The patient was assessed as Fitzpatrick phototype III · a female patient in their mid-80s · a clinical photograph showing a skin lesion: 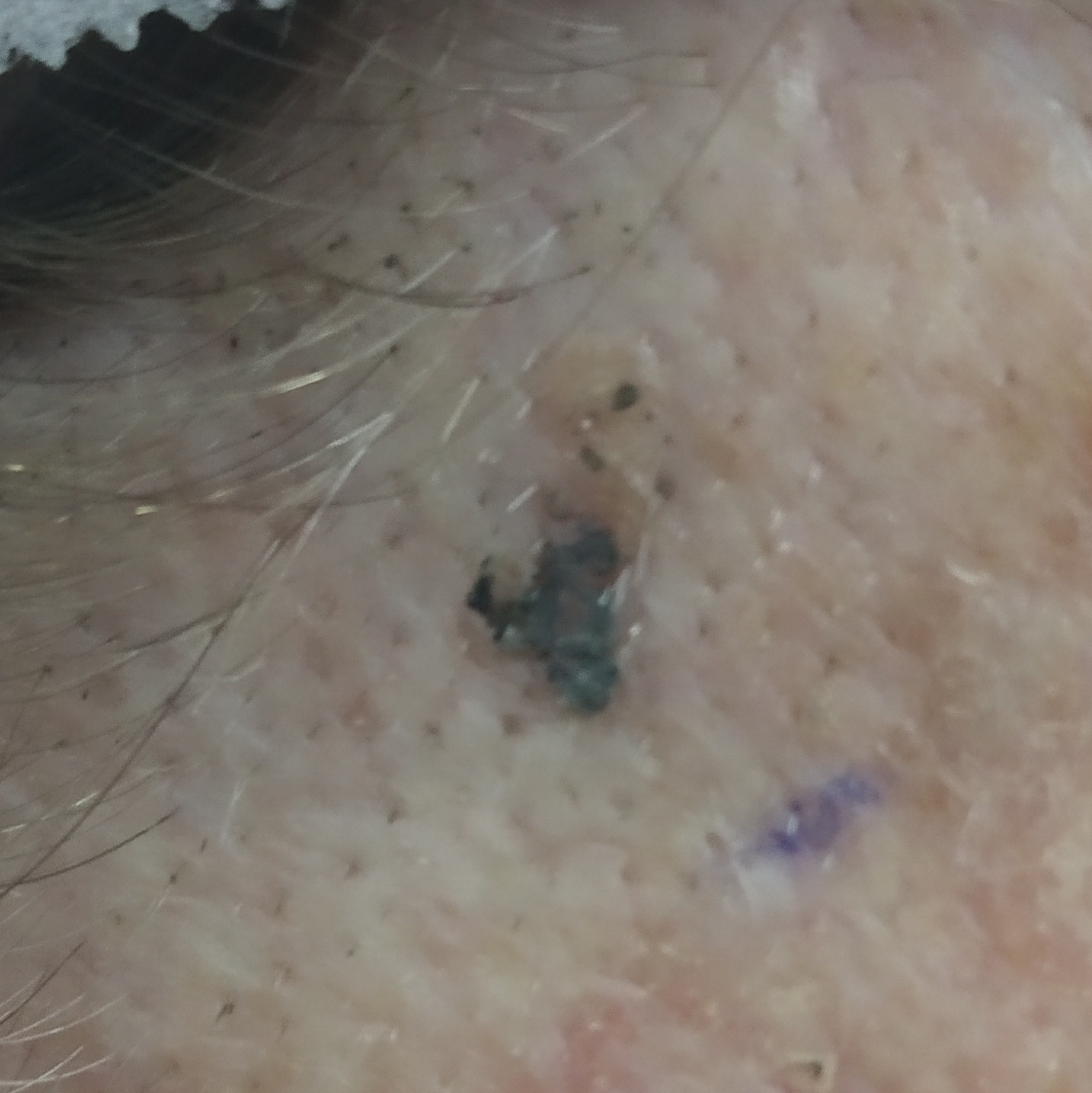Case summary:
The lesion involves the face. The lesion measures 3 × 3 mm.
Conclusion:
Histopathologically confirmed as a benign lesion — a seborrheic keratosis.